The patient reported no systemic symptoms. Male subject, age 40–49. Texture is reported as flat. Reported lesion symptoms include pain and burning. The photograph was taken at an angle. Self-categorized by the patient as a rash: 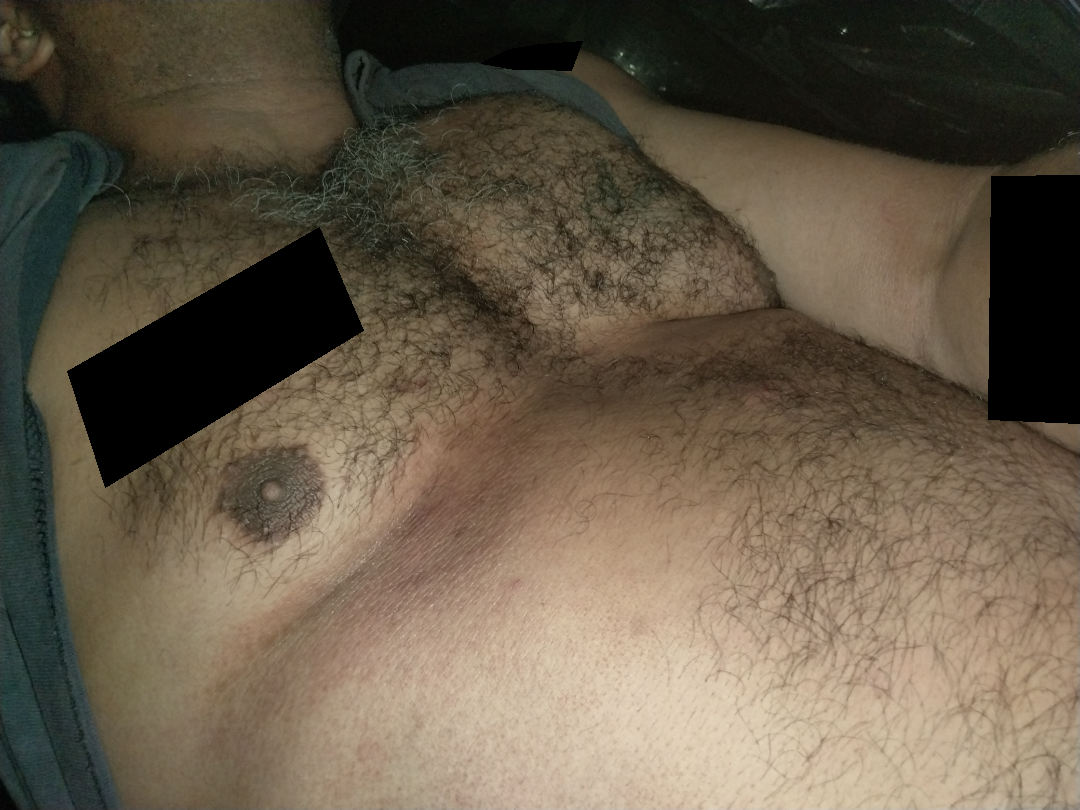Acanthosis nigricans and Eczema were considered with similar weight; less probable is Intertrigo; a remote consideration is Contact dermatitis, NOS.